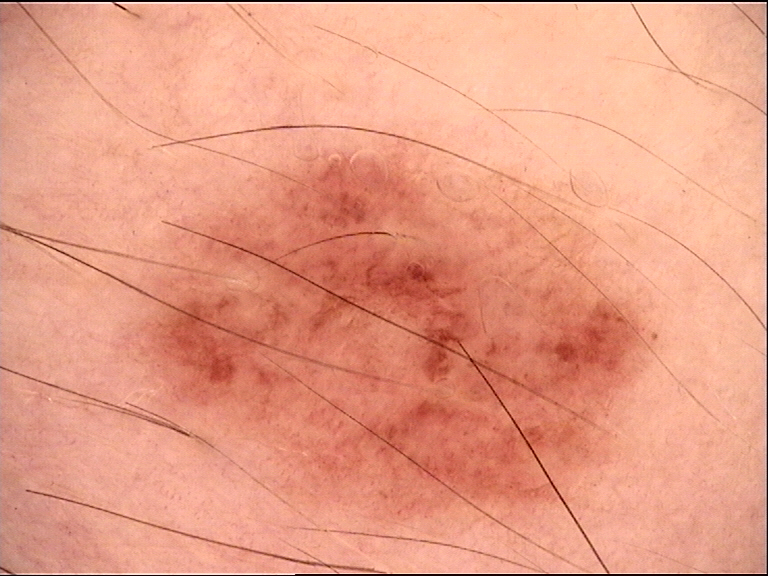{
  "image": "dermatoscopy",
  "diagnosis": {
    "name": "dysplastic junctional nevus",
    "code": "jd",
    "malignancy": "benign",
    "super_class": "melanocytic",
    "confirmation": "expert consensus"
  }
}